The photo was captured at a distance, the subject is a female aged 30–39 — 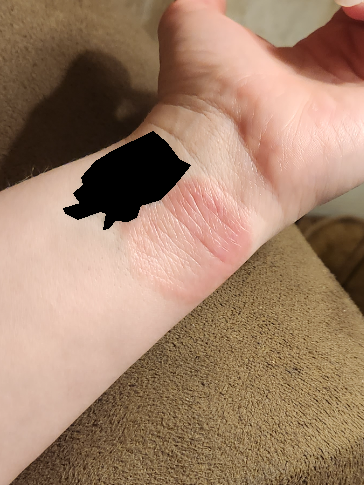The patient indicates the condition has been present for one to three months. The patient considered this a rash. The lesion is described as flat and rough or flaky. Associated systemic symptoms include mouth sores. On photographic review by a dermatologist: Chronic dermatitis, NOS and Allergic Contact Dermatitis were considered with similar weight.